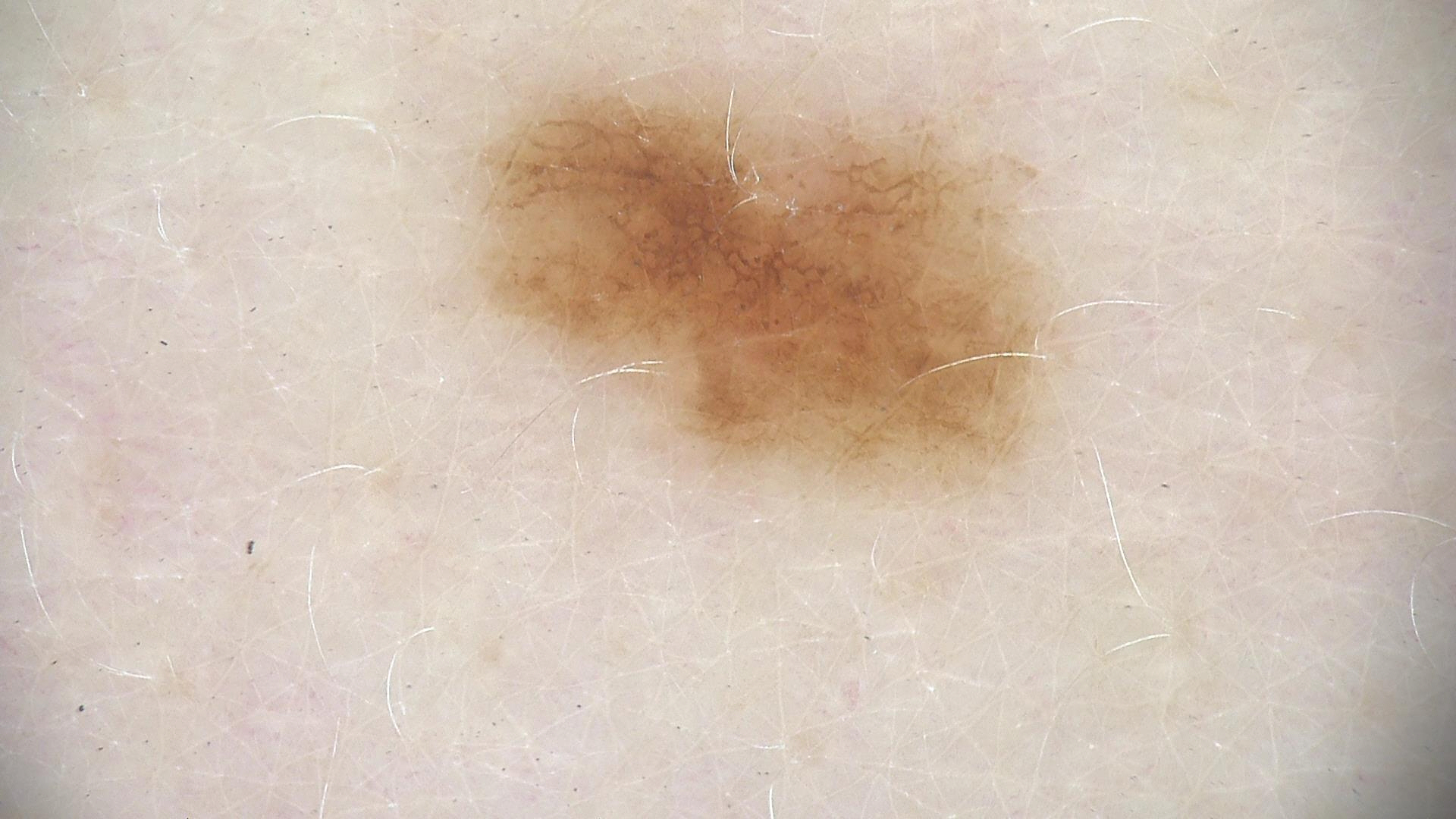diagnostic label: dysplastic junctional nevus (expert consensus).